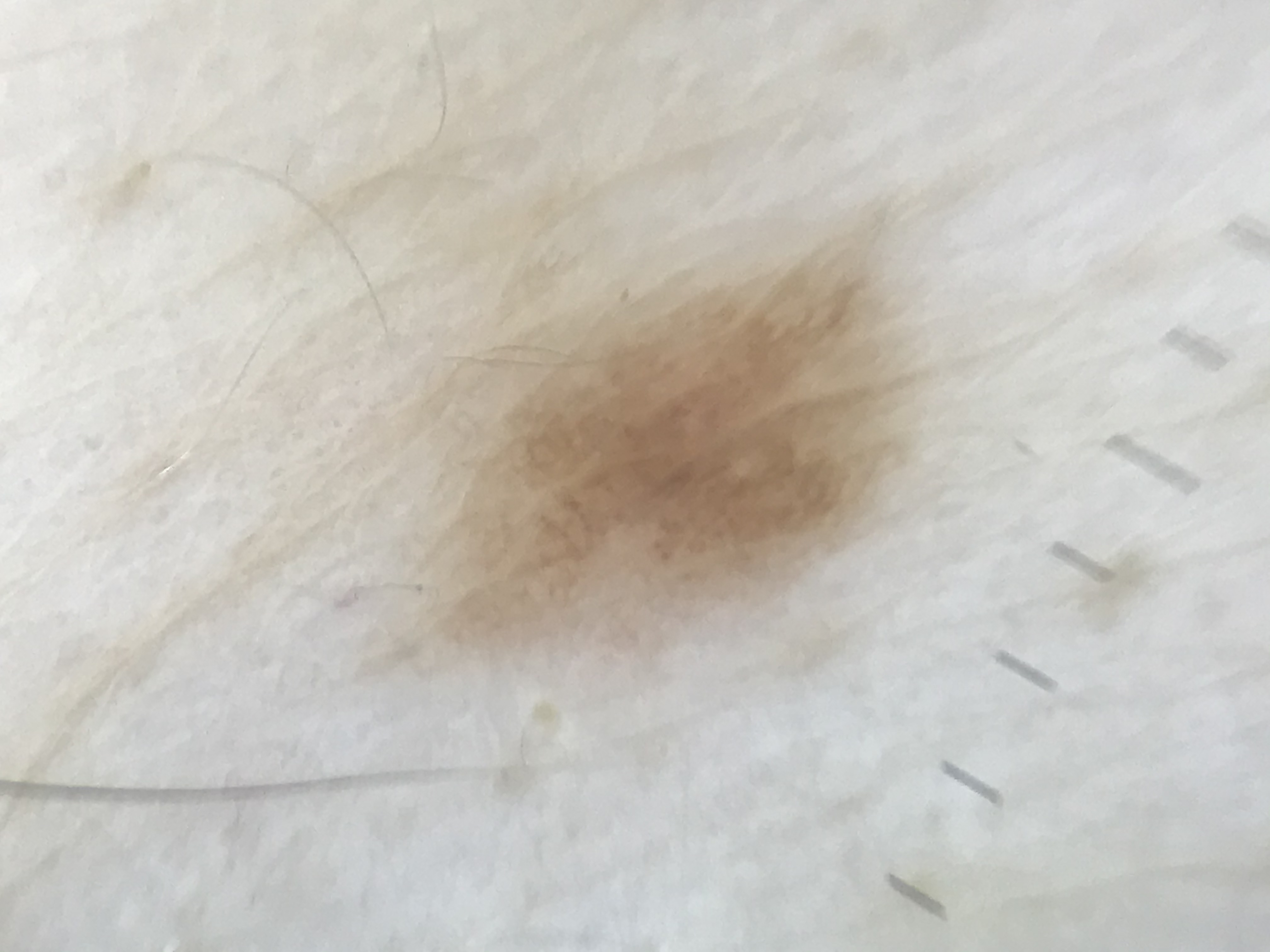Findings:
– diagnosis · junctional nevus (expert consensus)